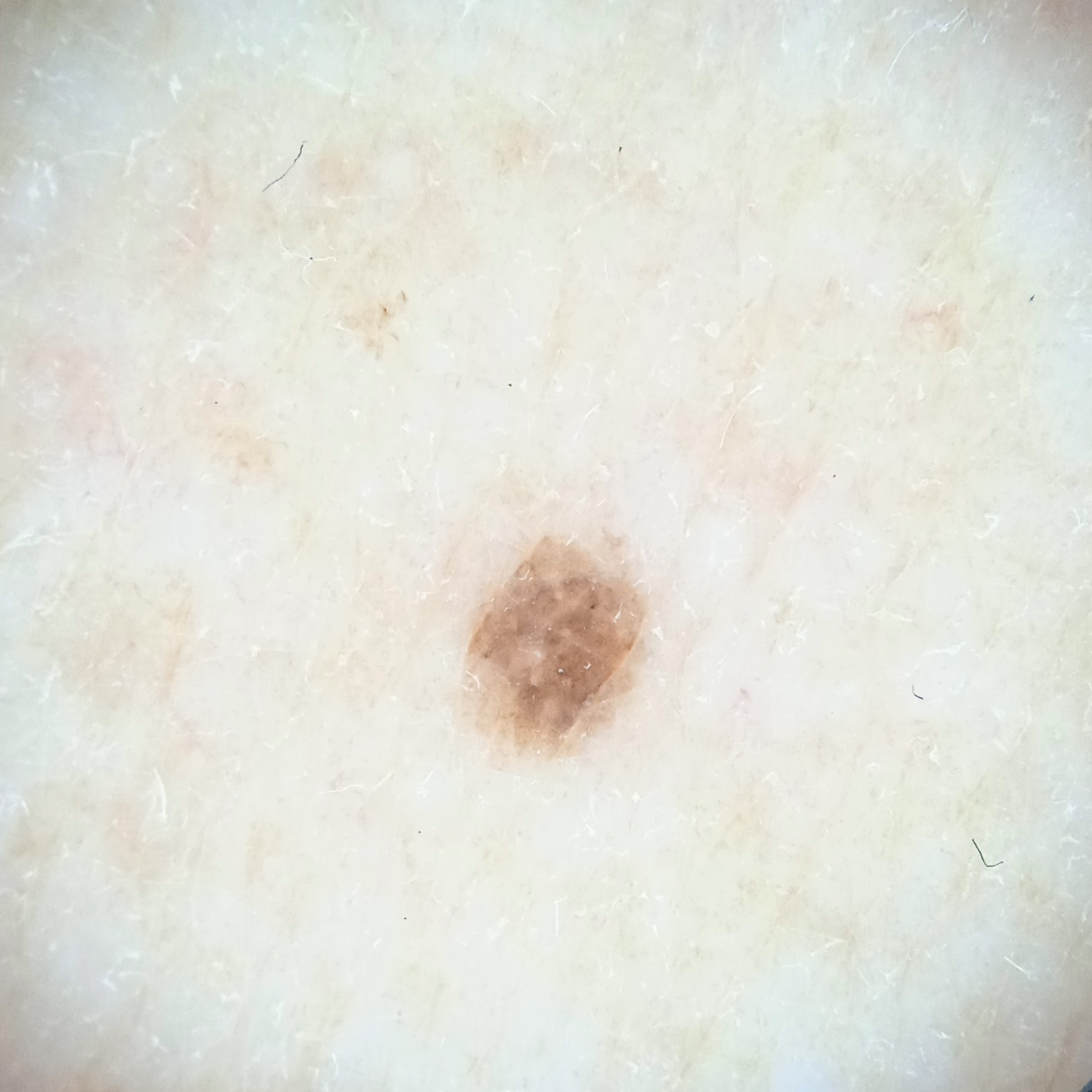assessment: melanocytic nevus (dermatologist consensus).